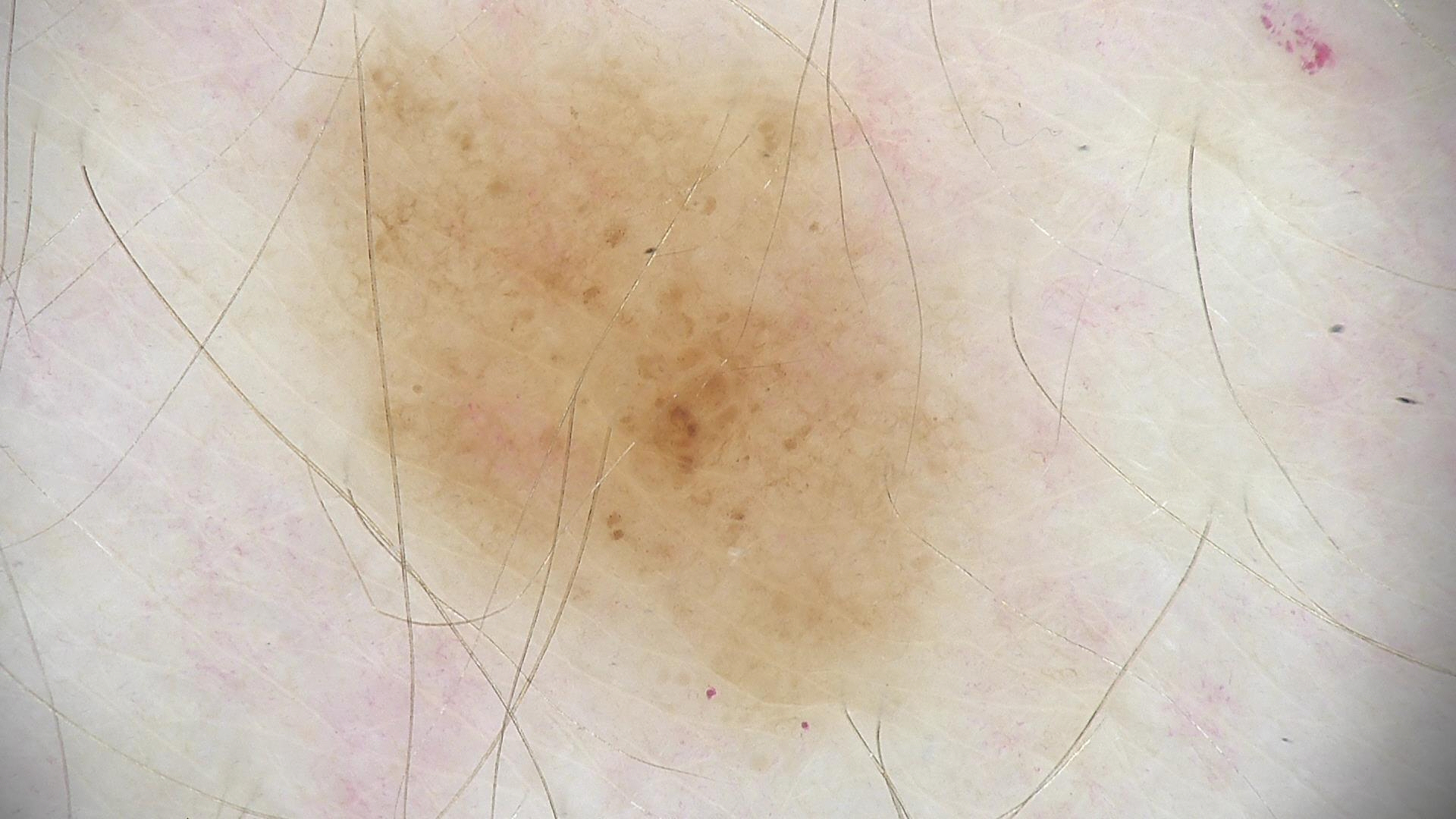• assessment — dysplastic junctional nevus (expert consensus)